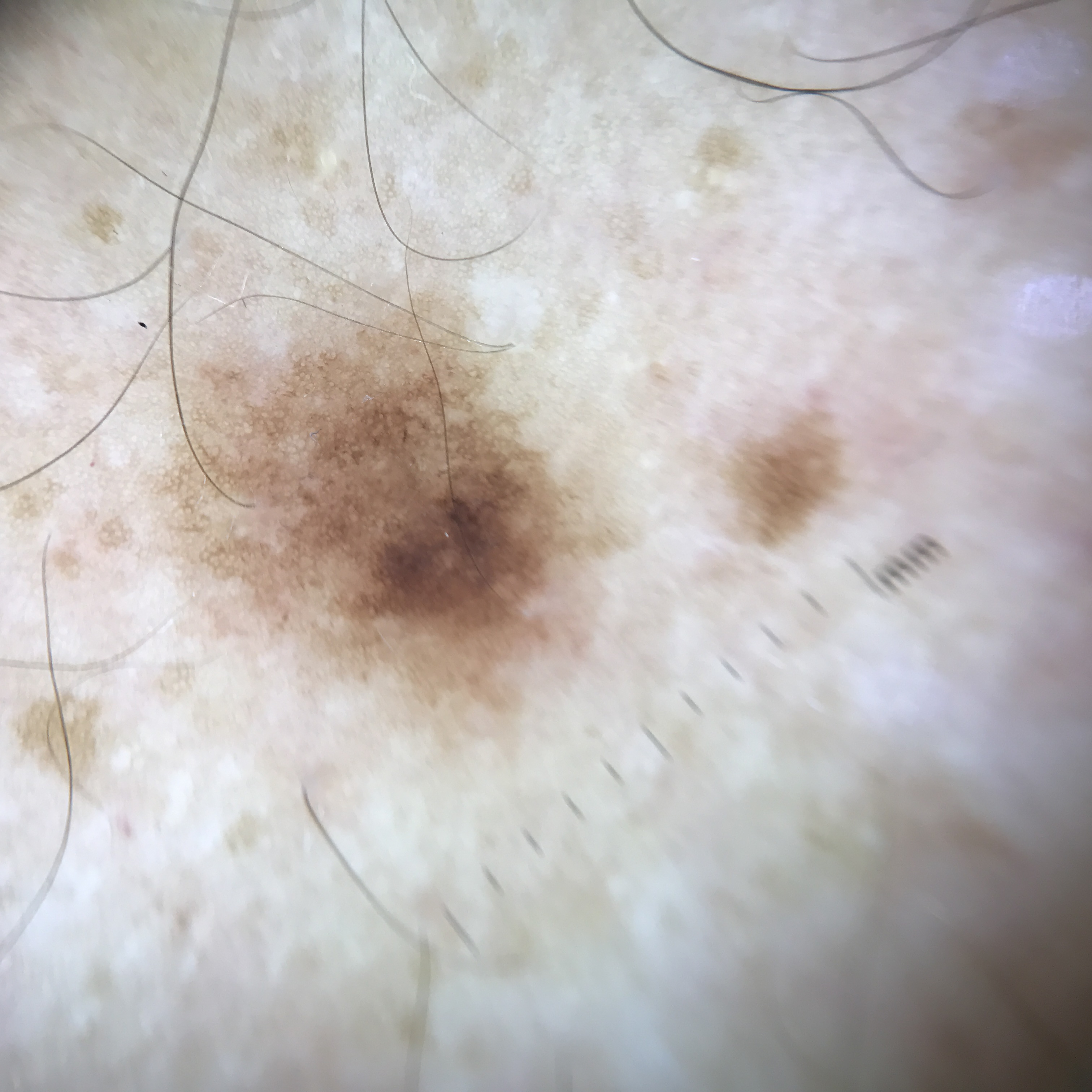modality = dermoscopy; diagnostic label = dysplastic junctional nevus (expert consensus).